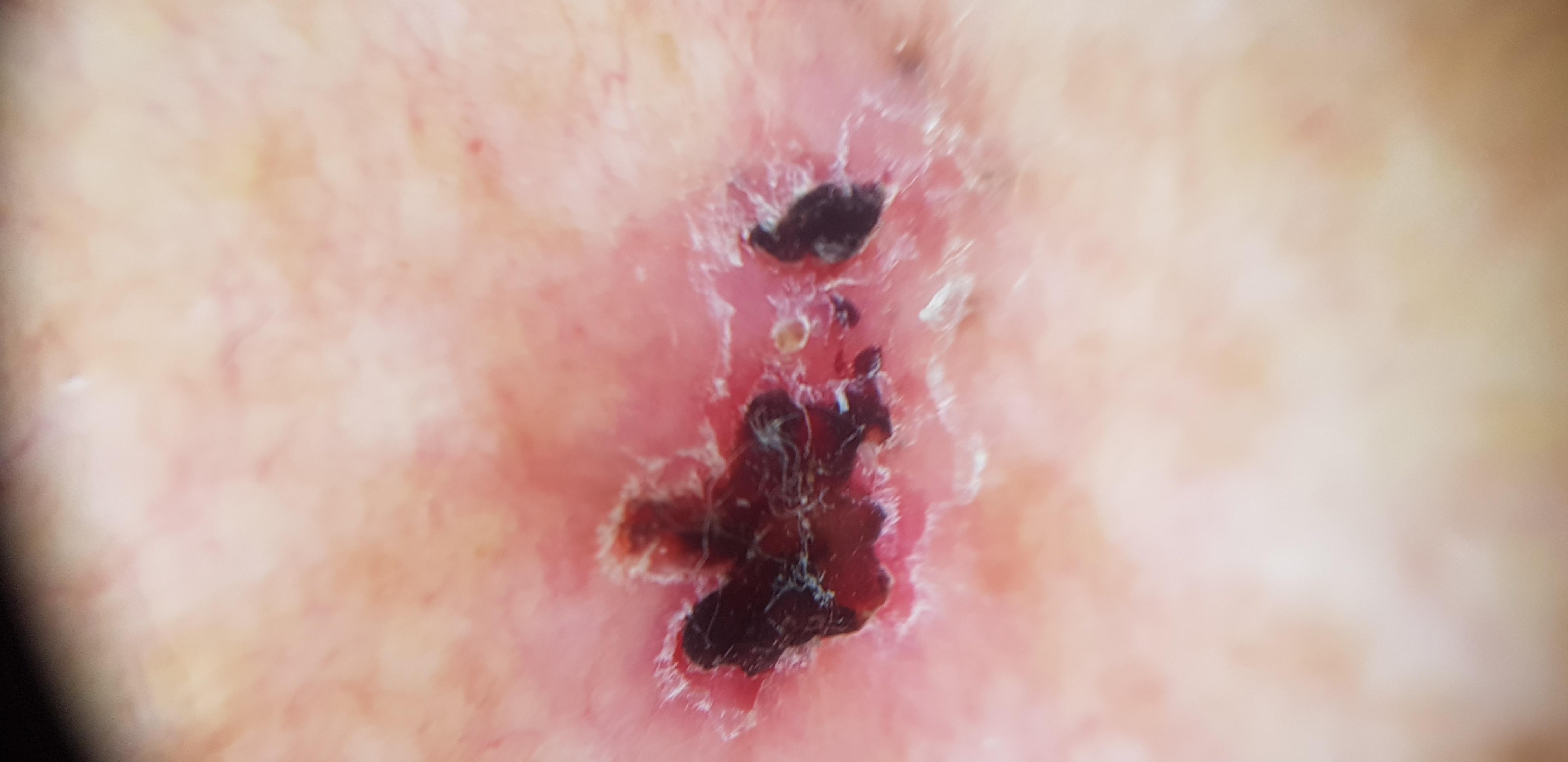diagnosis = Basal cell carcinoma (biopsy-proven).